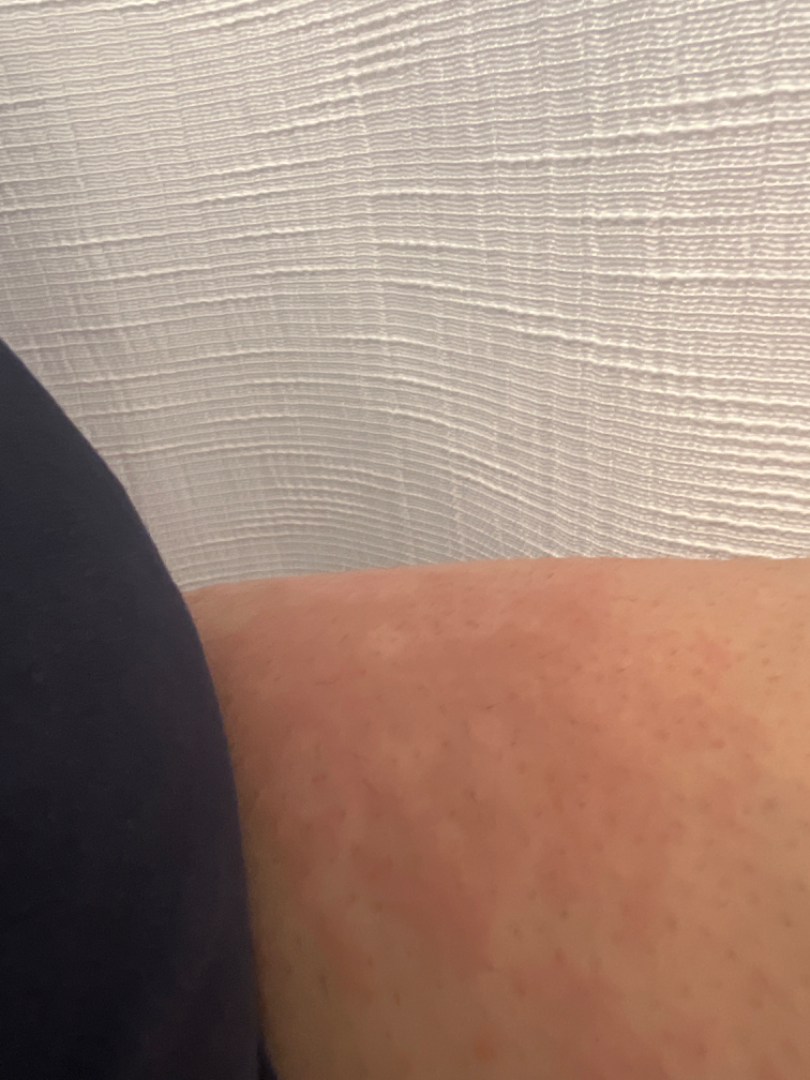Present for one to three months. The patient reports the lesion is raised or bumpy. Self-categorized by the patient as a rash. The leg is involved. The patient reports itching and darkening. The photo was captured at an angle. The contributor is a female aged 18–29. Reviewed remotely by three dermatologists: most consistent with Urticaria.